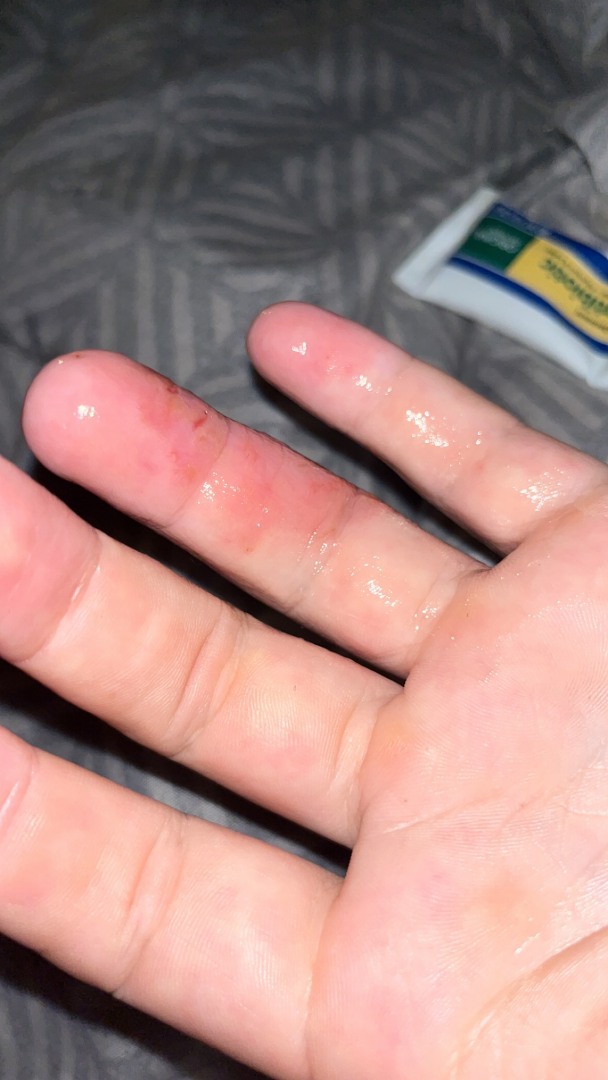Findings:
- assessment · ungradable on photographic review
- affected area · back of the hand and palm
- framing · close-up
- patient · male, age 18–29